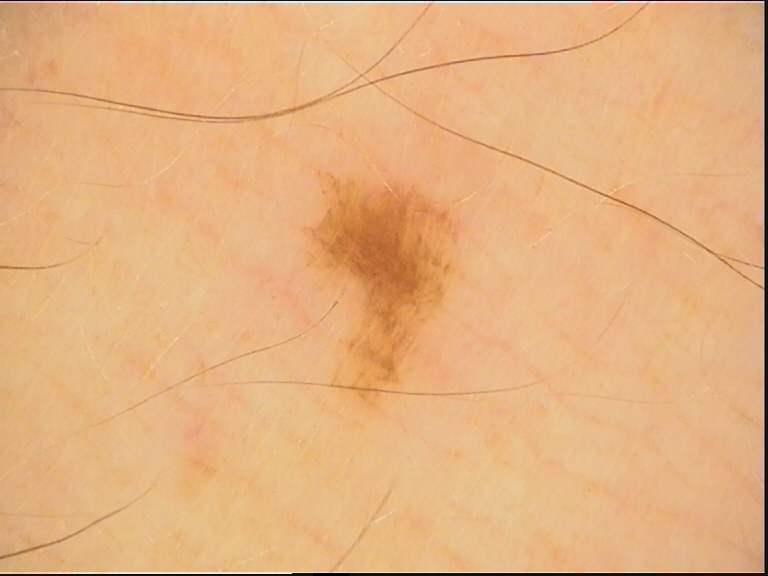• image — dermatoscopy
• diagnosis — acral dysplastic junctional nevus (expert consensus)